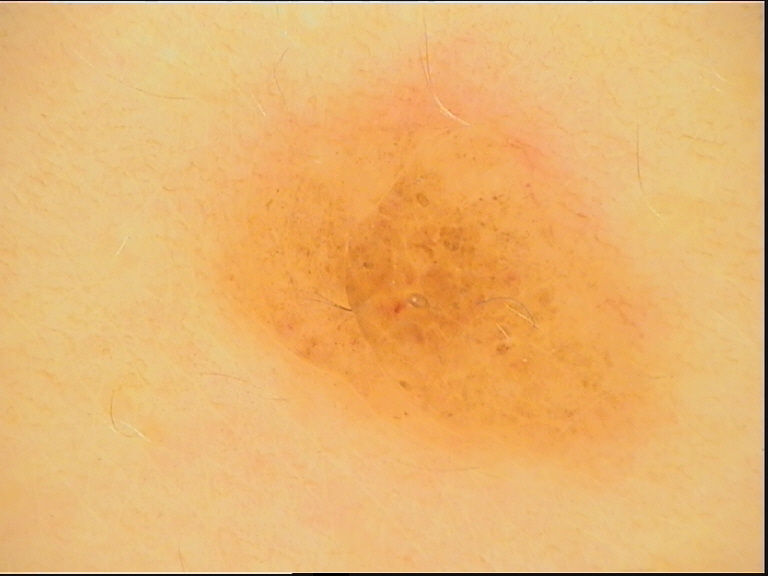A dermoscopic close-up of a skin lesion.
Labeled as a banal lesion — a compound nevus.